Located on the leg. Close-up view.
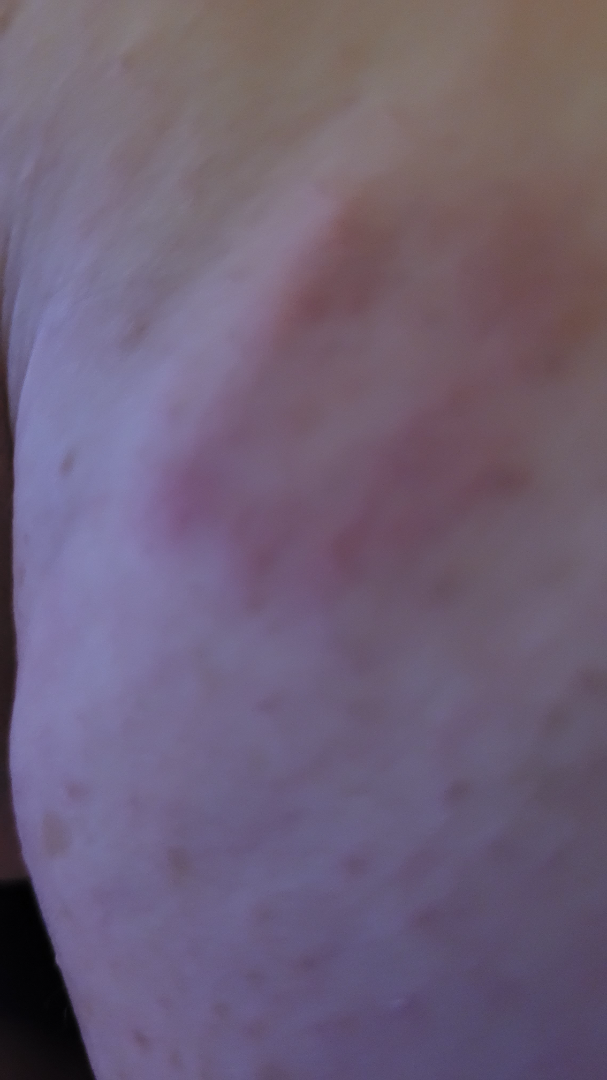{"assessment": "indeterminate"}